The photograph is a close-up of the affected area — 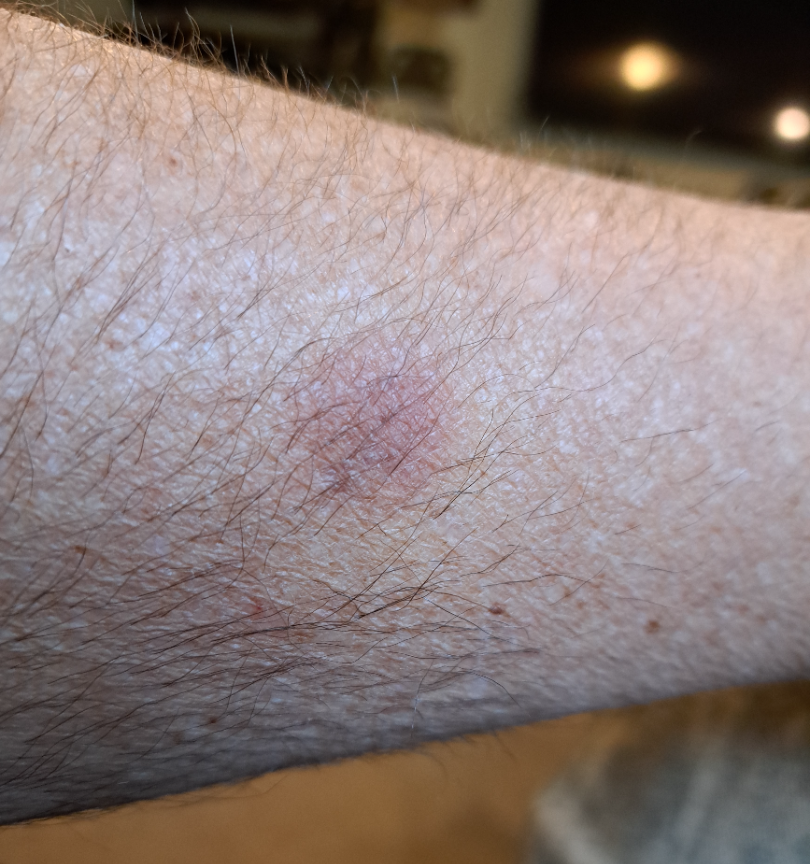Findings: The case was indeterminate on photographic review.